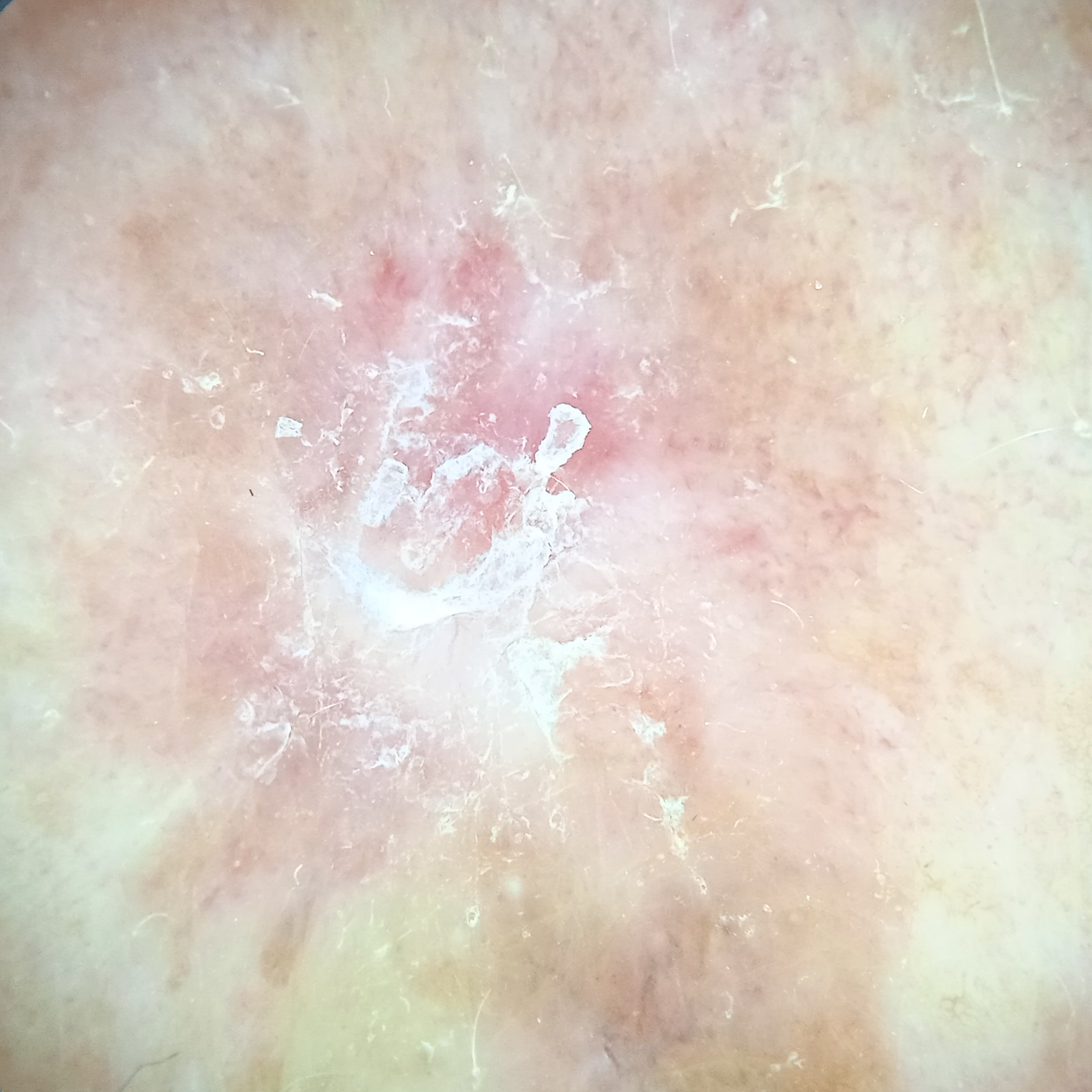<lesion>
<patient>
<age>62</age>
<sex>male</sex>
</patient>
<sun_reaction>skin reddens with sun exposure</sun_reaction>
<referral>research study (no referral diagnosis)</referral>
<image>dermoscopic image</image>
<lesion_location>the back</lesion_location>
<lesion_size>
<diameter_mm>13.8</diameter_mm>
</lesion_size>
<diagnosis>
<name>squamous cell carcinoma</name>
<malignancy>malignant</malignancy>
</diagnosis>
</lesion>